The lesion involves the front of the torso and arm; the patient indicates pain; the condition has been present for about one day; the patient indicates the lesion is raised or bumpy; the patient described the issue as a rash; this is a close-up image — 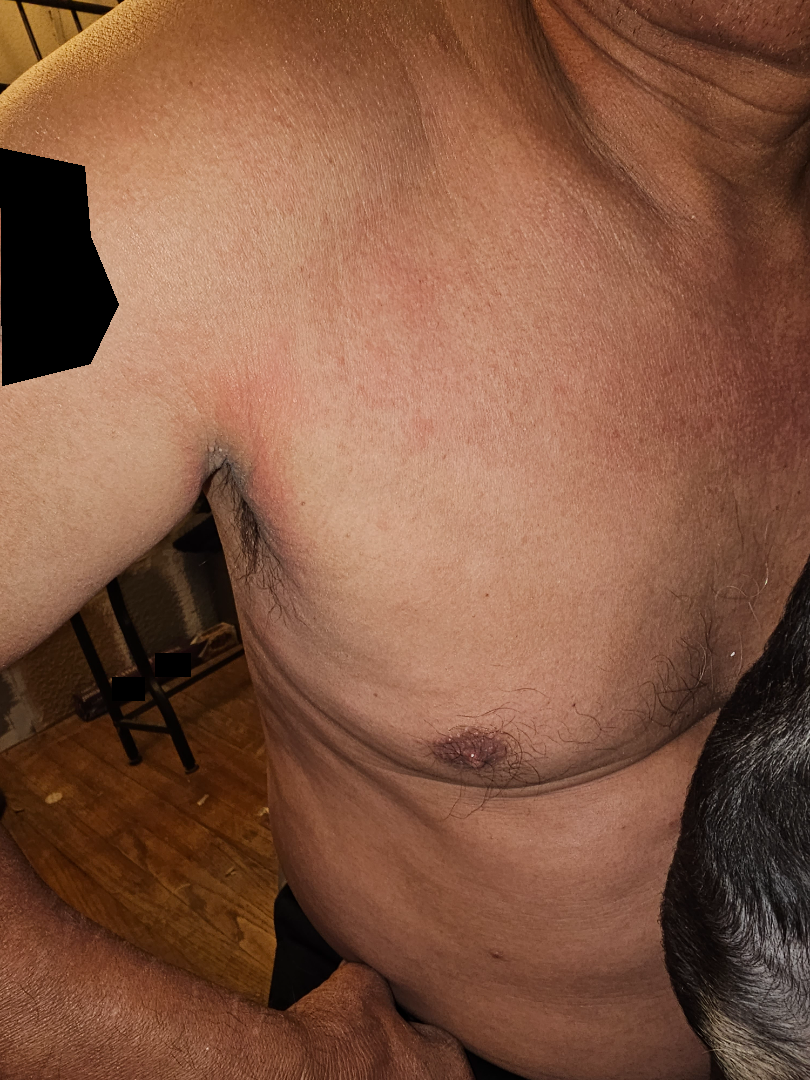{
  "differential": {
    "tied_lead": [
      "Eczema",
      "Hypersensitivity",
      "Allergic Contact Dermatitis"
    ]
  }
}